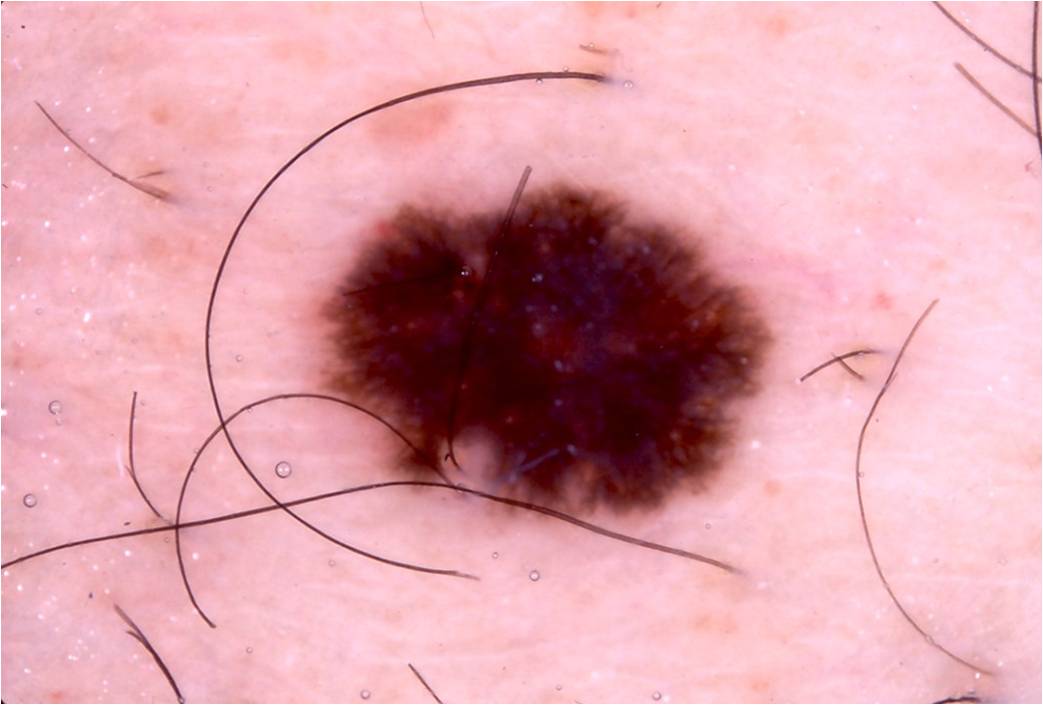A dermoscopic image of a skin lesion. A male patient approximately 15 years of age. In (x1, y1, x2, y2) order, the lesion occupies the region 316/177/779/536. The lesion takes up about 17% of the image. On dermoscopy, the lesion shows pigment network and streaks, with no negative network, globules, or milia-like cysts. The clinical diagnosis was a melanocytic nevus, a benign skin lesion.